A close-up photograph · texture is reported as rough or flaky and raised or bumpy · the leg is involved · the patient notes the condition has been present for less than one week: 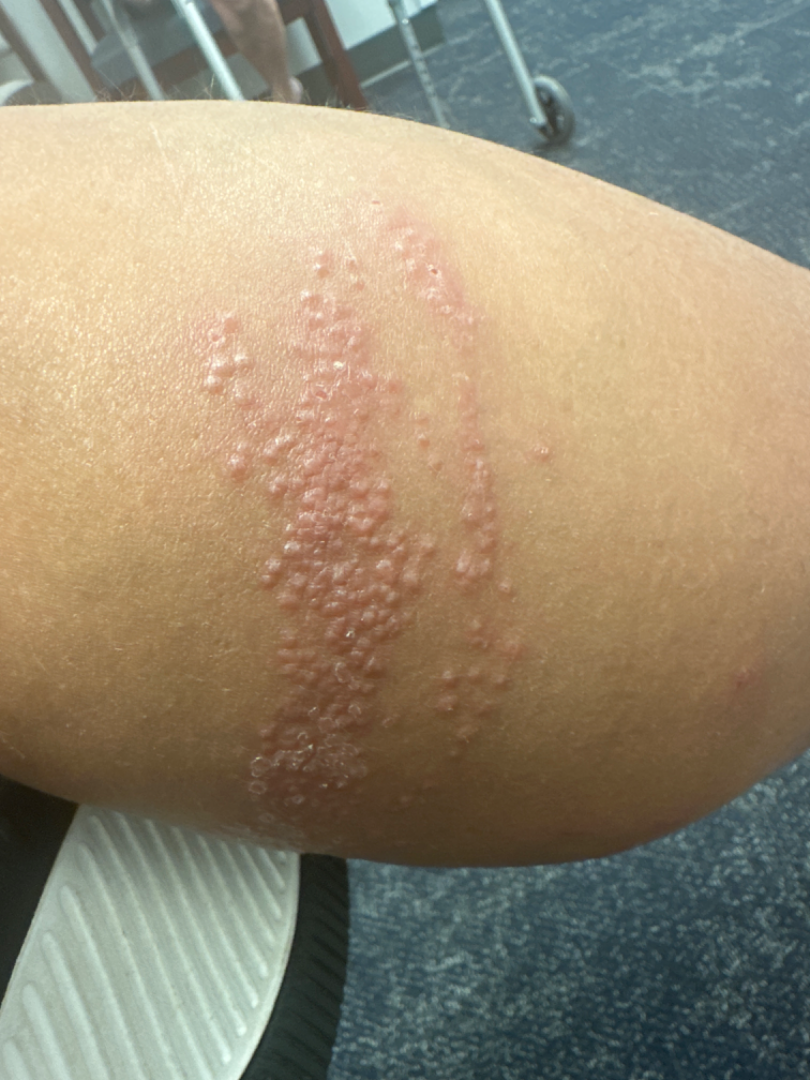{
  "assessment": "not assessable"
}